An image taken at an angle:
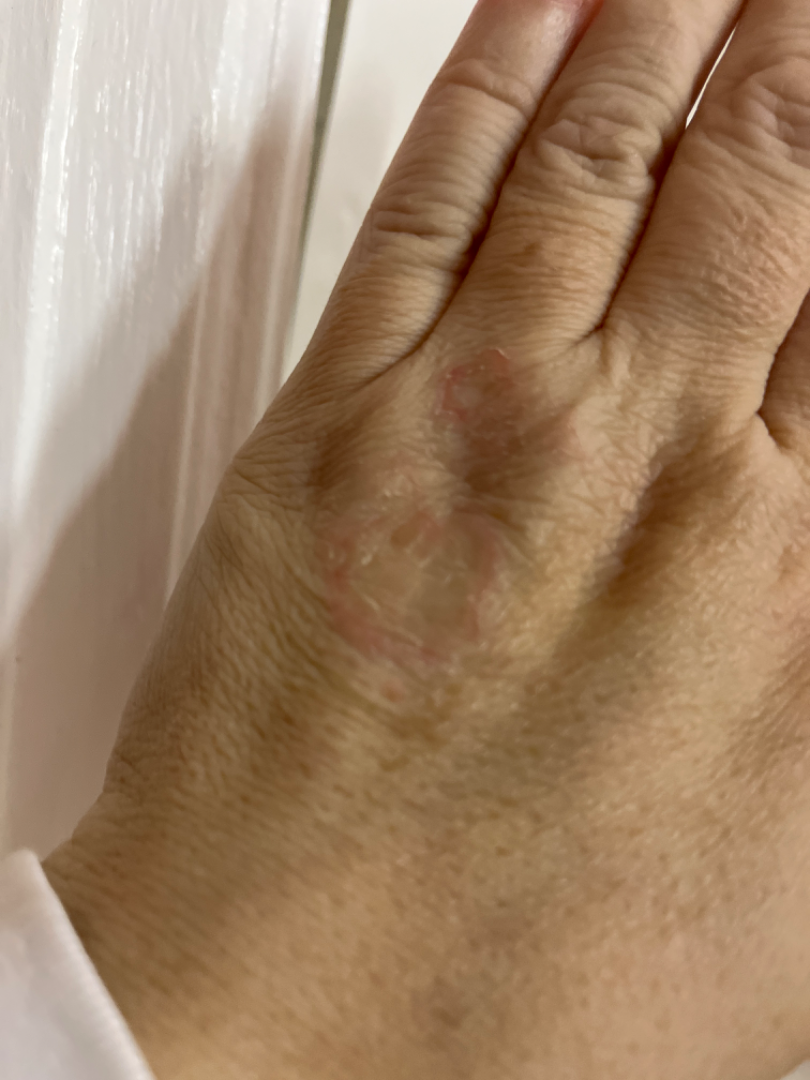differential:
  tied_lead:
    - Tinea
    - Eczema